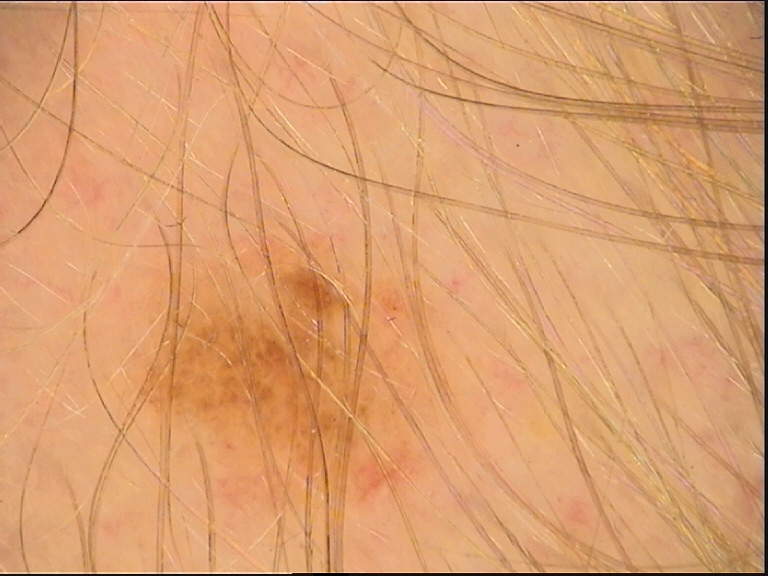Findings:
- diagnostic label: dysplastic junctional nevus (expert consensus)